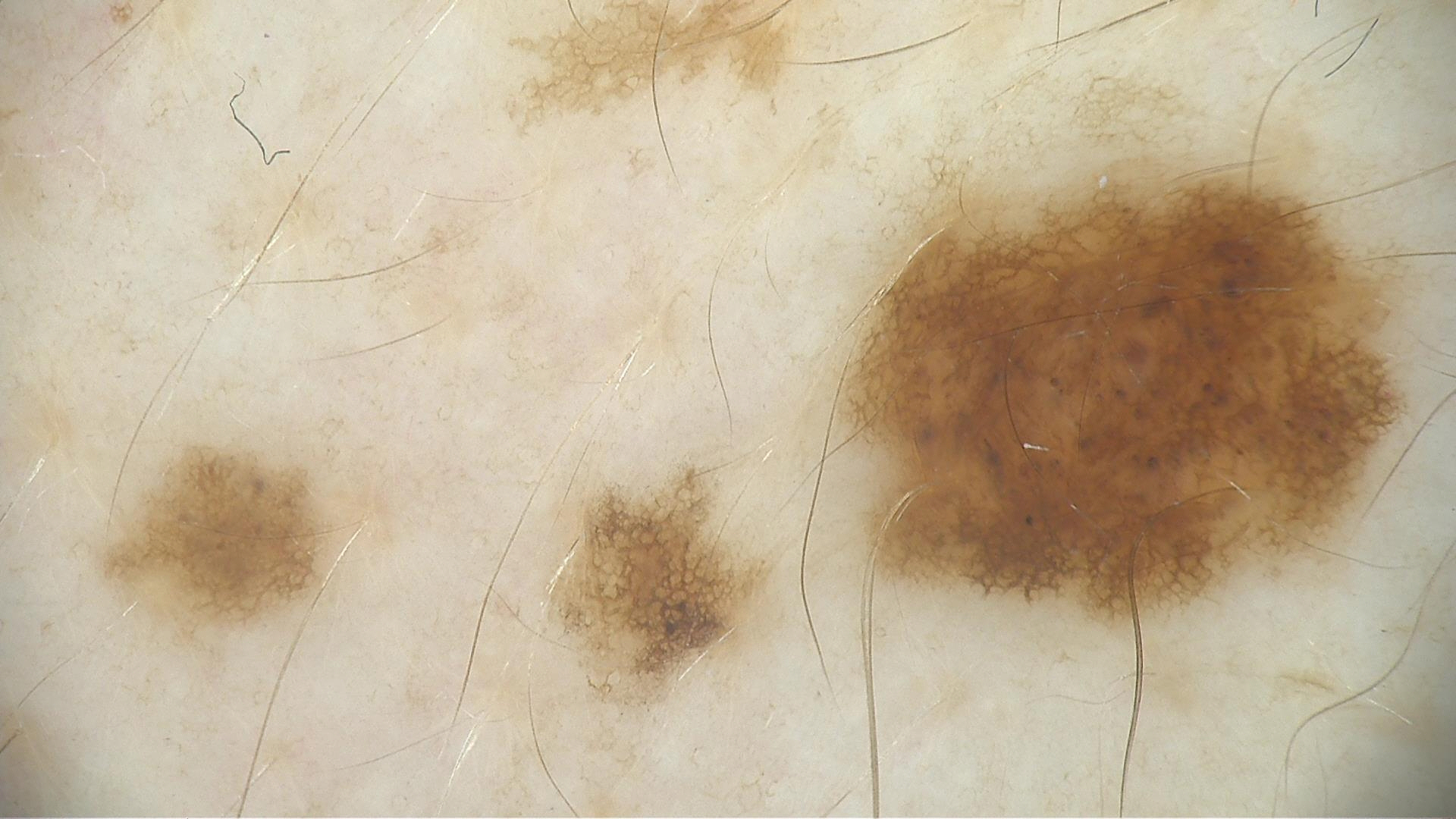• modality: dermoscopy
• assessment: dysplastic junctional nevus (expert consensus)